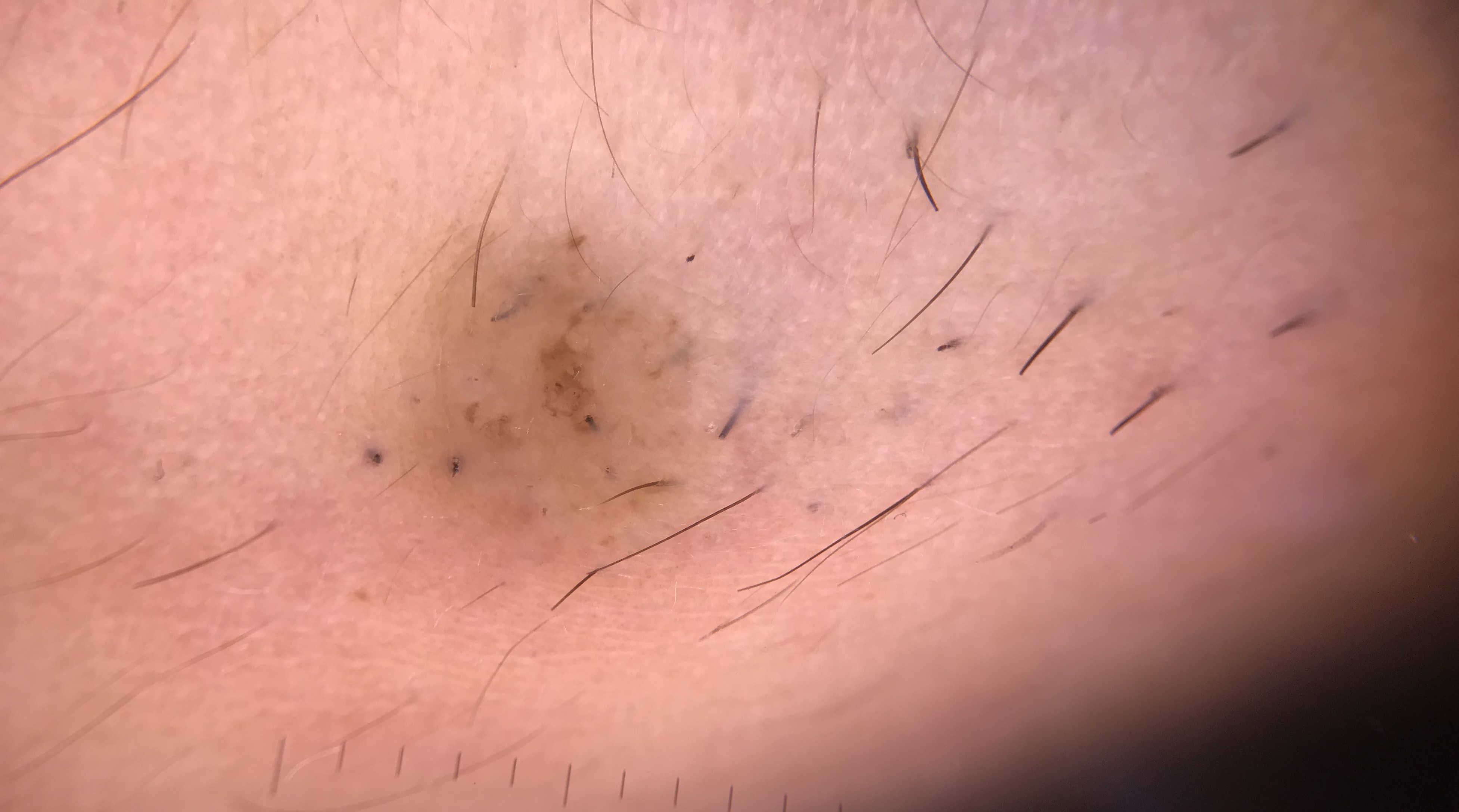The diagnosis was a Miescher nevus.